A female subject aged around 70. A dermatoscopic image of a skin lesion:
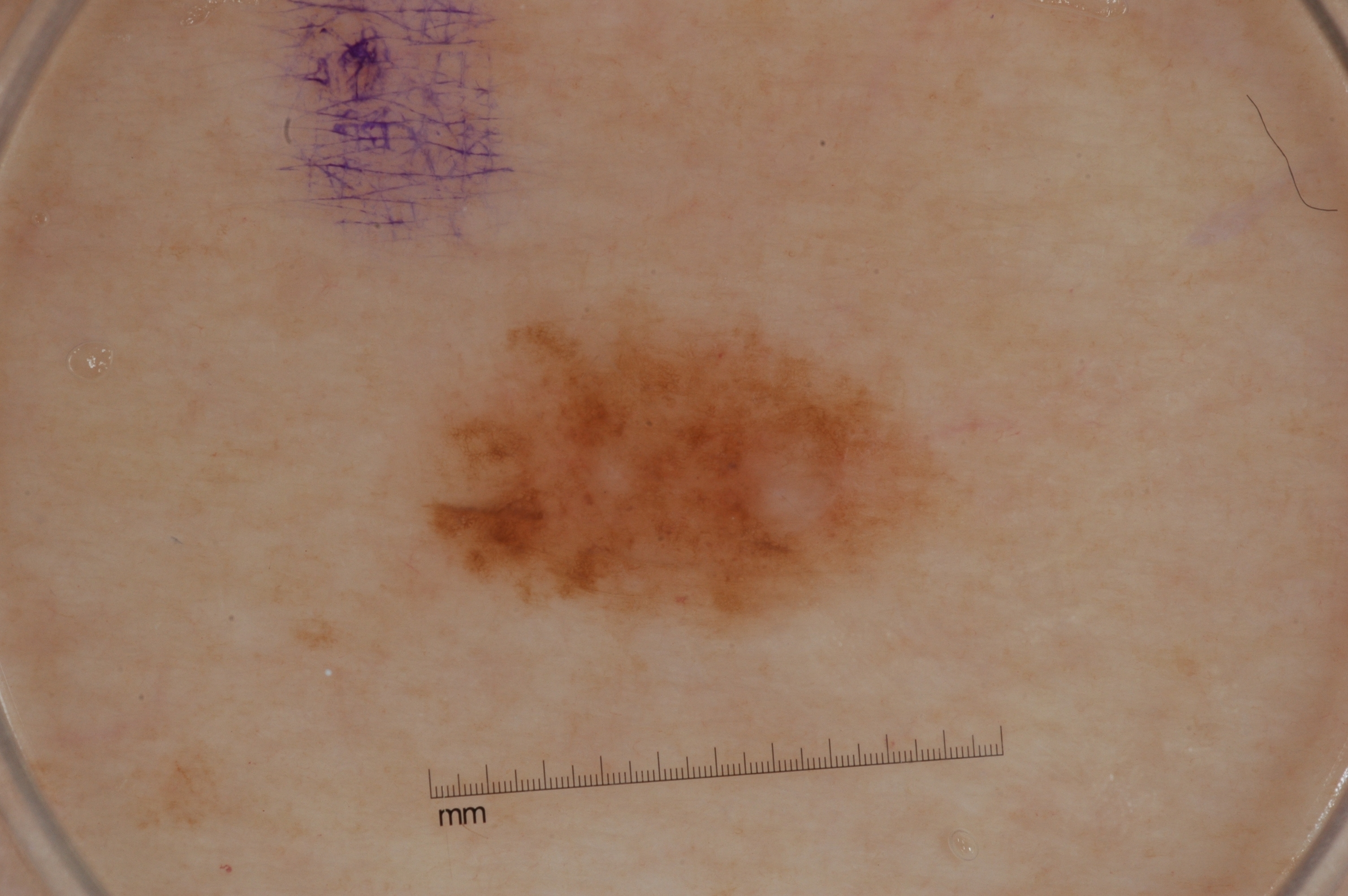size = moderate | features = pigment network and milia-like cysts; absent: streaks and negative network | bounding box = [422, 308, 937, 623] | assessment = a melanocytic nevus.